The photo was captured at an angle — 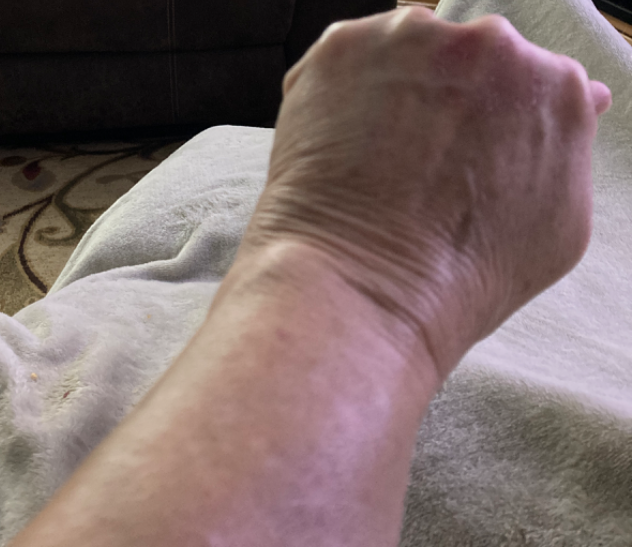The reviewing dermatologist's impression was: Tinea and Eczema were each considered, in no particular order.